Located on the leg · the contributor is female · close-up view:
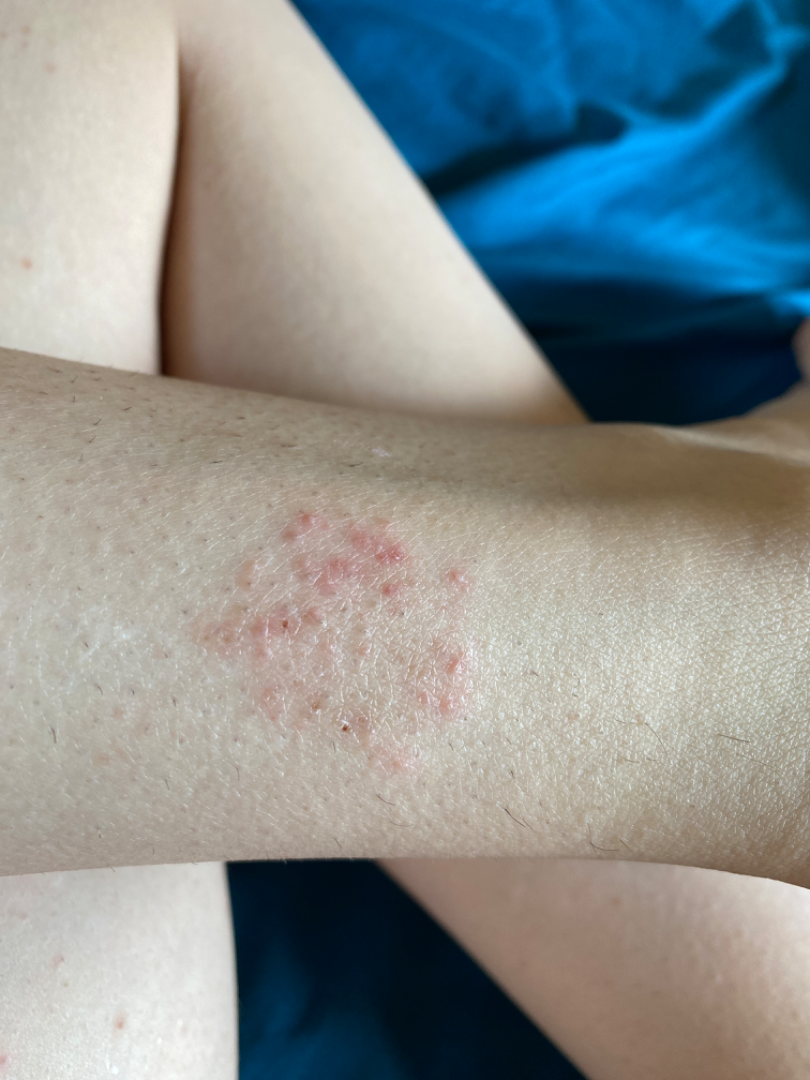reported symptoms: itching and enlargement
systemic symptoms: none reported
duration: less than one week
skin tone: FST II; human graders estimated a Monk Skin Tone of 3
surface texture: raised or bumpy
impression: Eczema (primary); Contact dermatitis (considered)